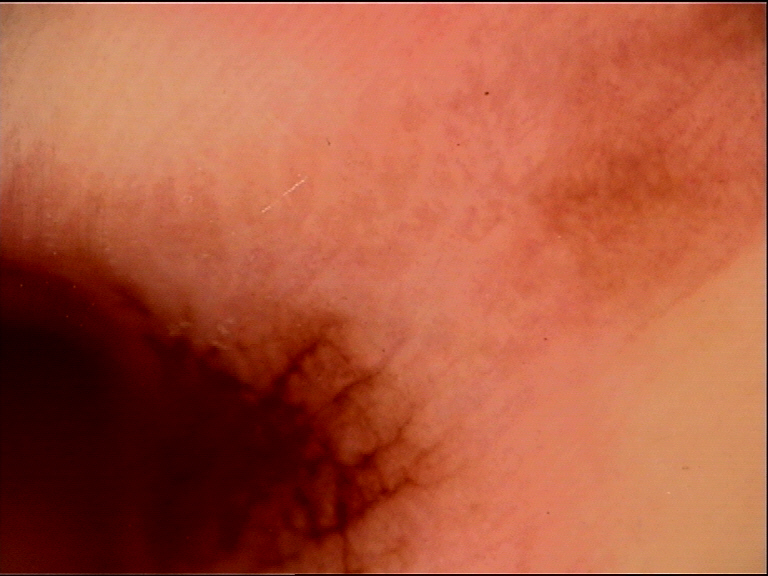Findings:
– imaging: dermatoscopy
– diagnosis: acral dysplastic junctional nevus (expert consensus)